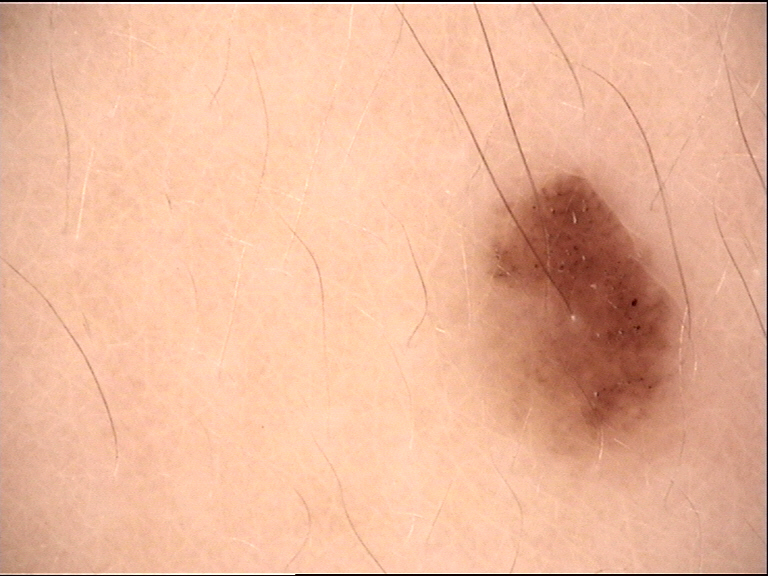Findings: A skin lesion imaged with a dermatoscope. Conclusion: Labeled as a banal lesion — a junctional nevus.